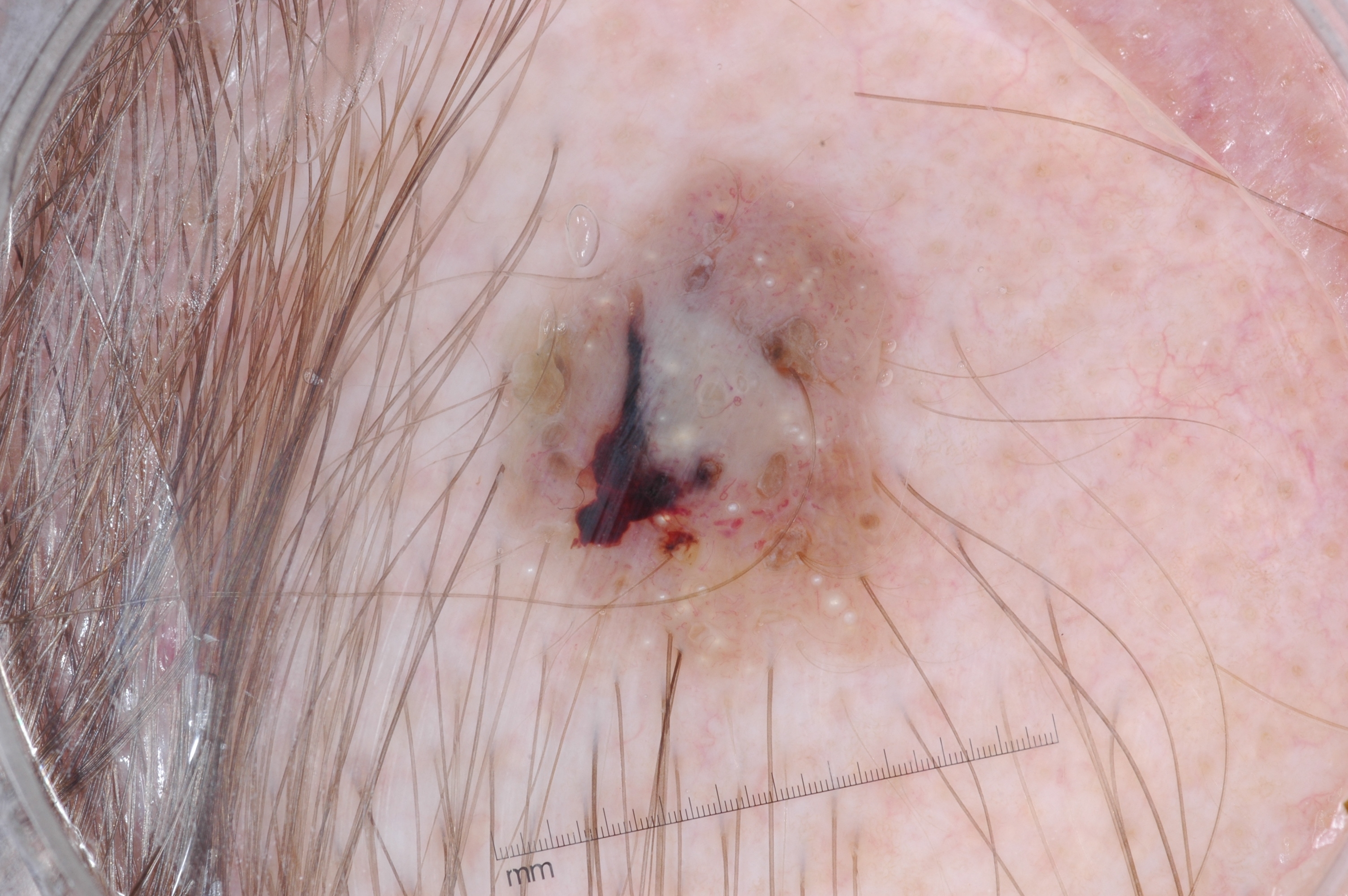  image:
    modality: dermoscopy
  patient:
    sex: male
    age_approx: 50
  lesion_extent:
    approx_field_fraction_pct: 12
  lesion_location:
    bbox_xyxy:
      - 495
      - 161
      - 916
      - 644
  dermoscopic_features:
    present:
      - milia-like cysts
    absent:
      - negative network
      - pigment network
      - streaks
  diagnosis:
    name: seborrheic keratosis
    malignancy: benign
    lineage: keratinocytic
    provenance: clinical